A dermoscopic close-up of a skin lesion. A female subject, in their 70s: 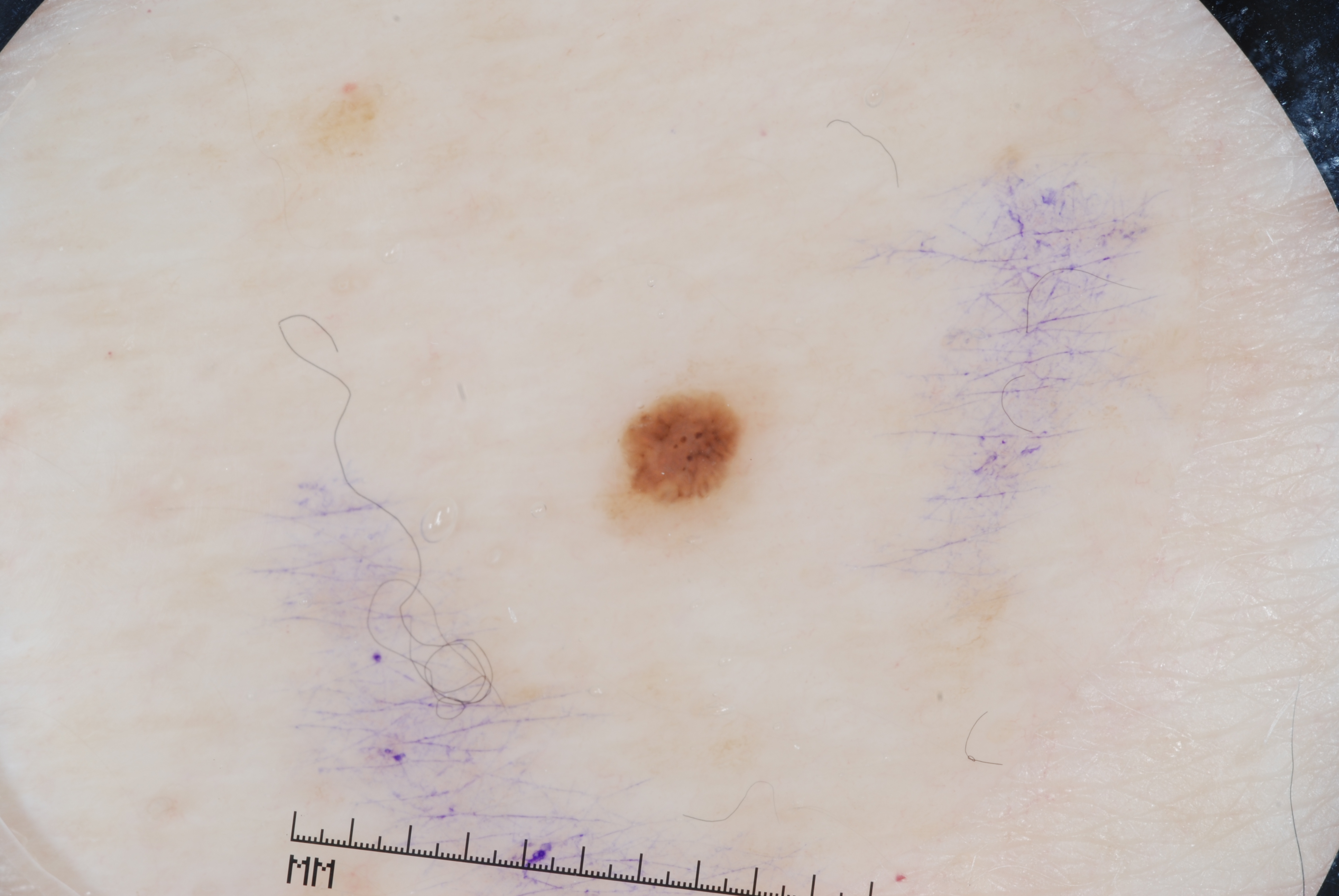Q: Where is the lesion in the image?
A: <bbox>617, 393, 753, 525</bbox>
Q: What does dermoscopy show?
A: milia-like cysts; absent: negative network, pigment network, and streaks
Q: What is this lesion?
A: a seborrheic keratosis